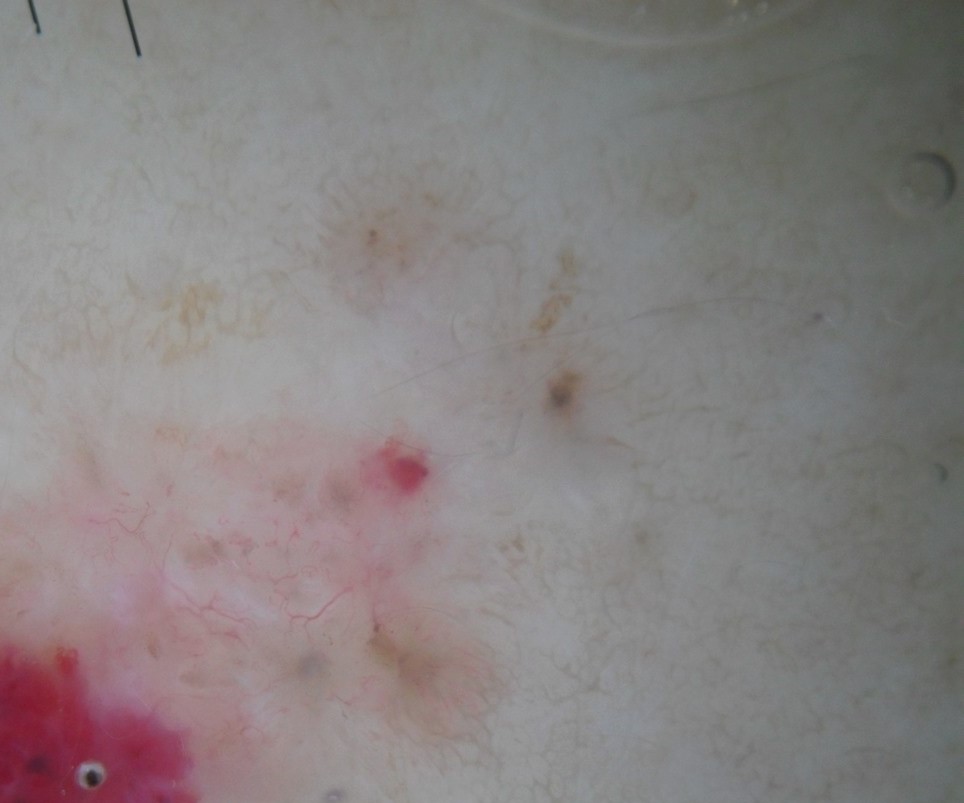The morphology is that of a keratinocytic lesion.
Histopathology confirmed a basal cell carcinoma.